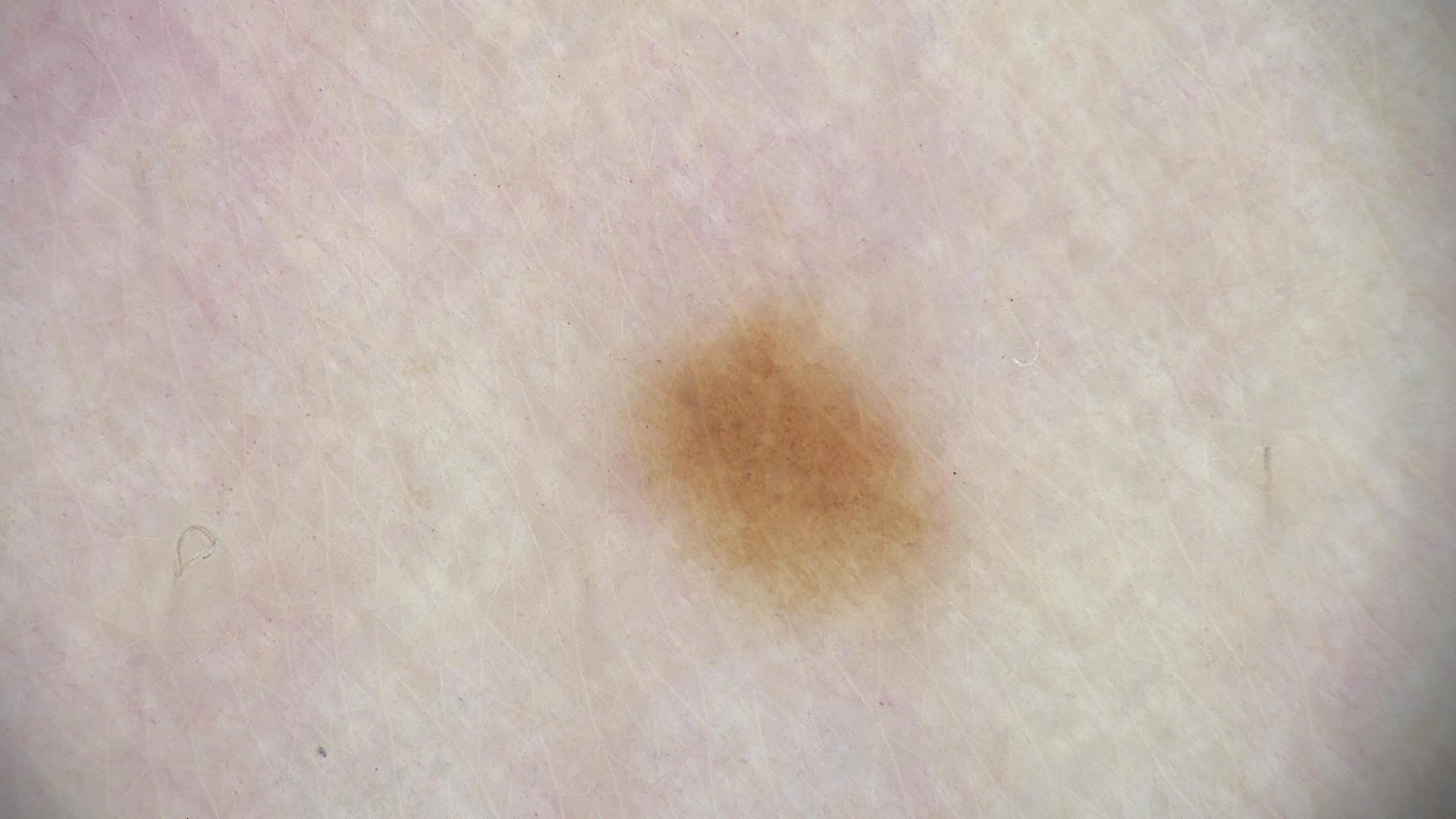A dermoscopy image of a single skin lesion. The morphology is that of a banal lesion. The diagnostic label was a junctional nevus.